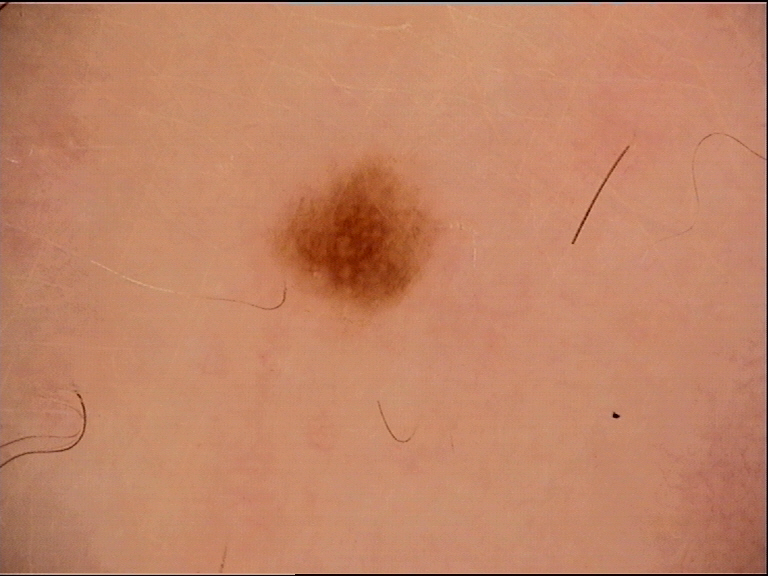A dermoscopic image of a skin lesion.
Consistent with a benign lesion — a dysplastic junctional nevus.